The arm is involved; the patient considered this a rash; an image taken at an angle; the patient indicates the lesion is raised or bumpy; reported lesion symptoms include bothersome appearance and itching: 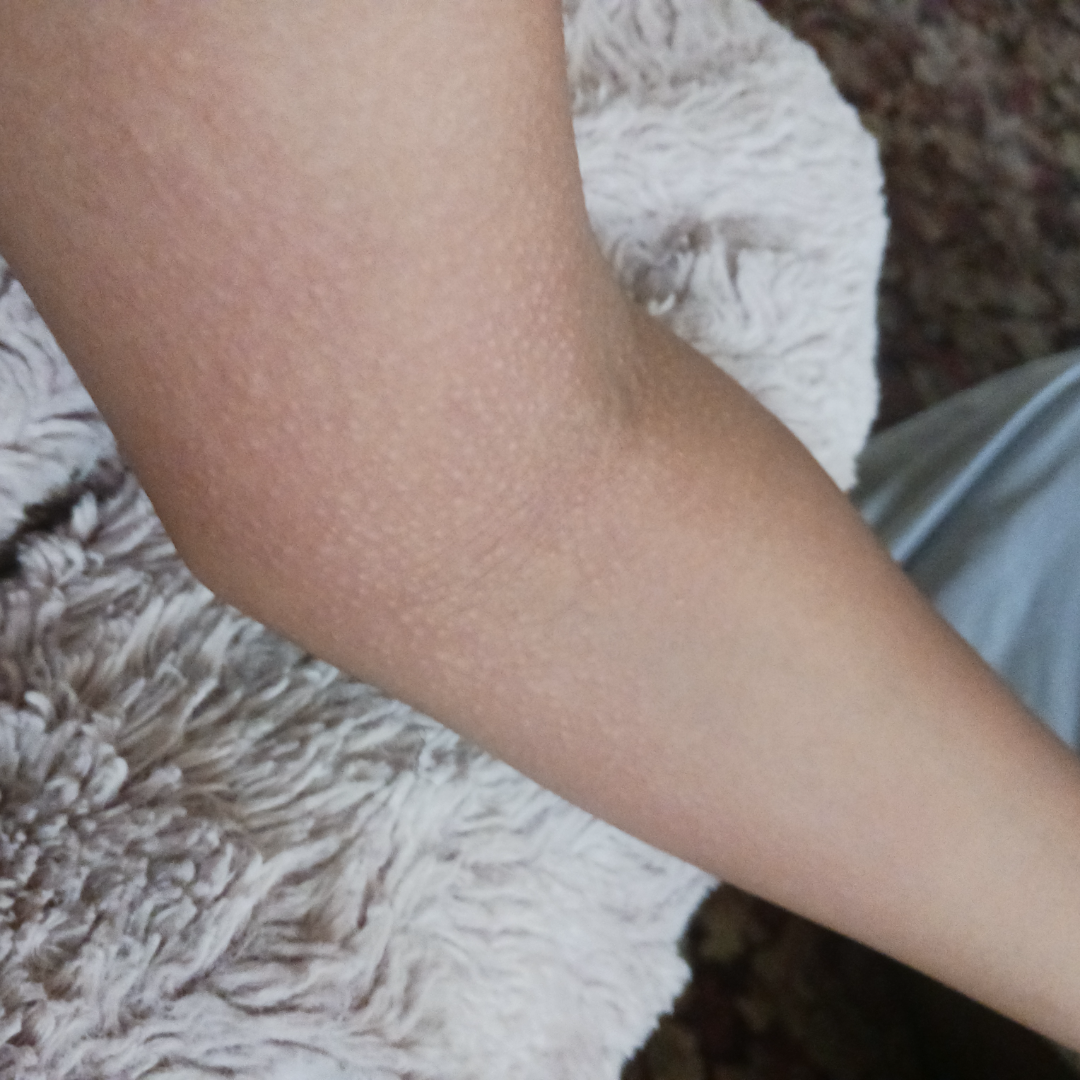dermatologist impression — most consistent with Eczema; a remote consideration is Lichen nitidus; lower on the differential is Urticaria; less likely is Allergic Contact Dermatitis